Dermoscopy of a skin lesion.
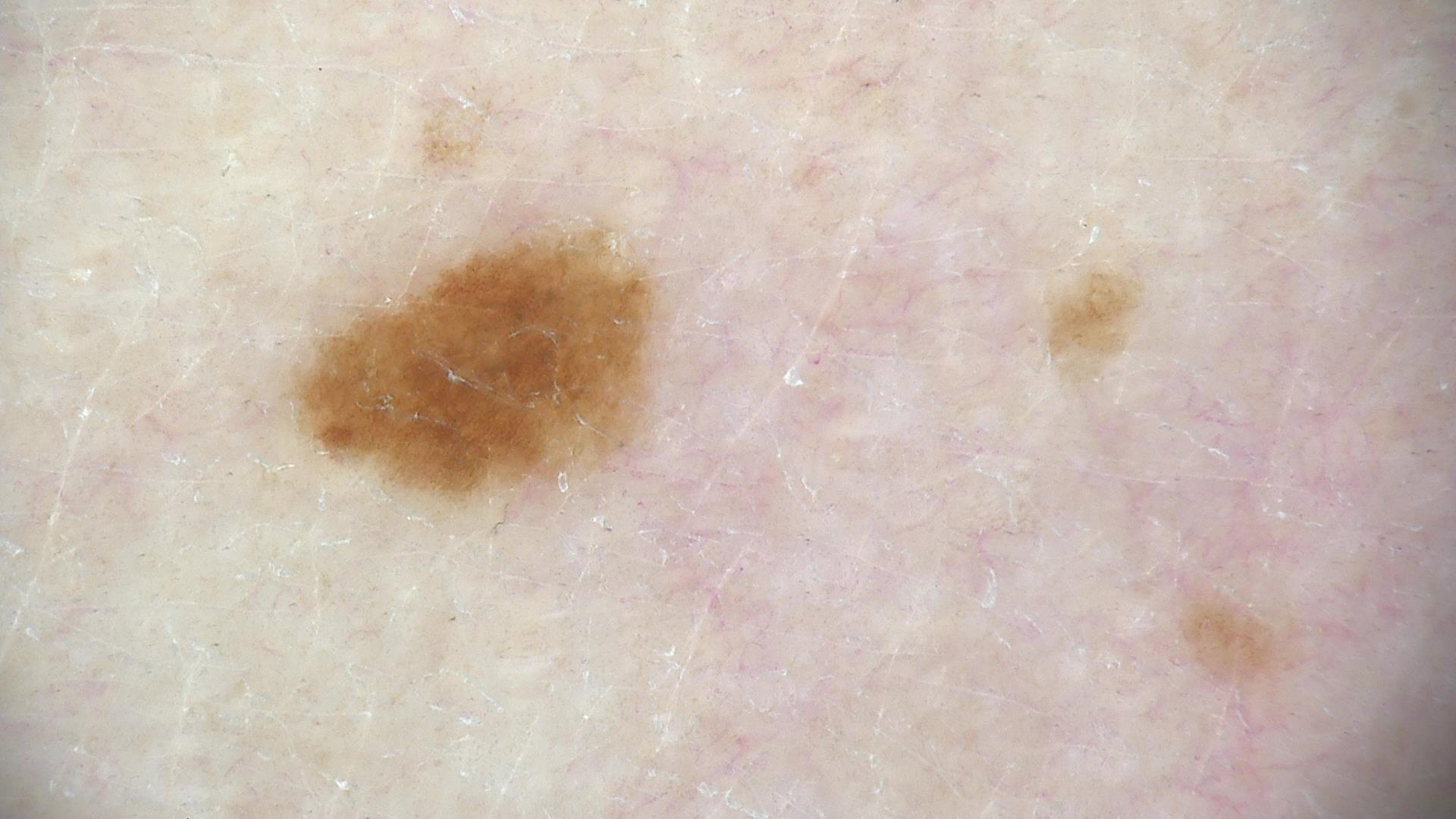The morphology is that of a banal lesion.
Classified as a junctional nevus.